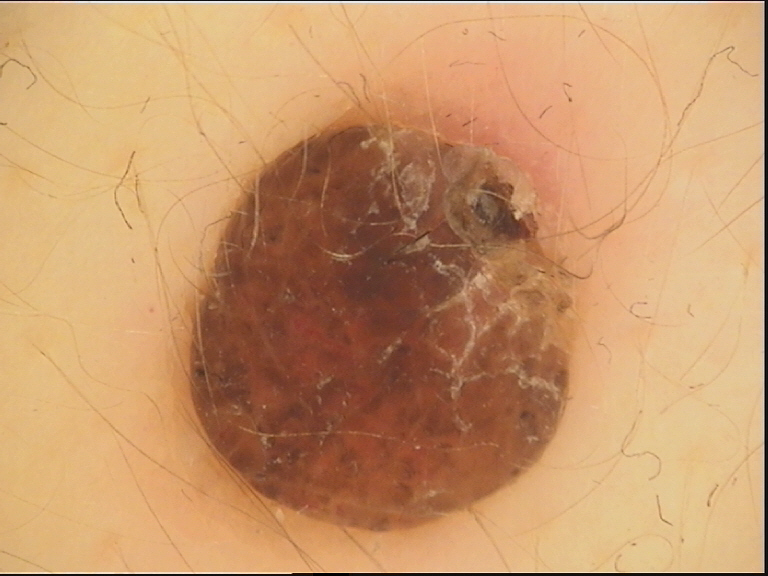Diagnosed as a dermal nevus.